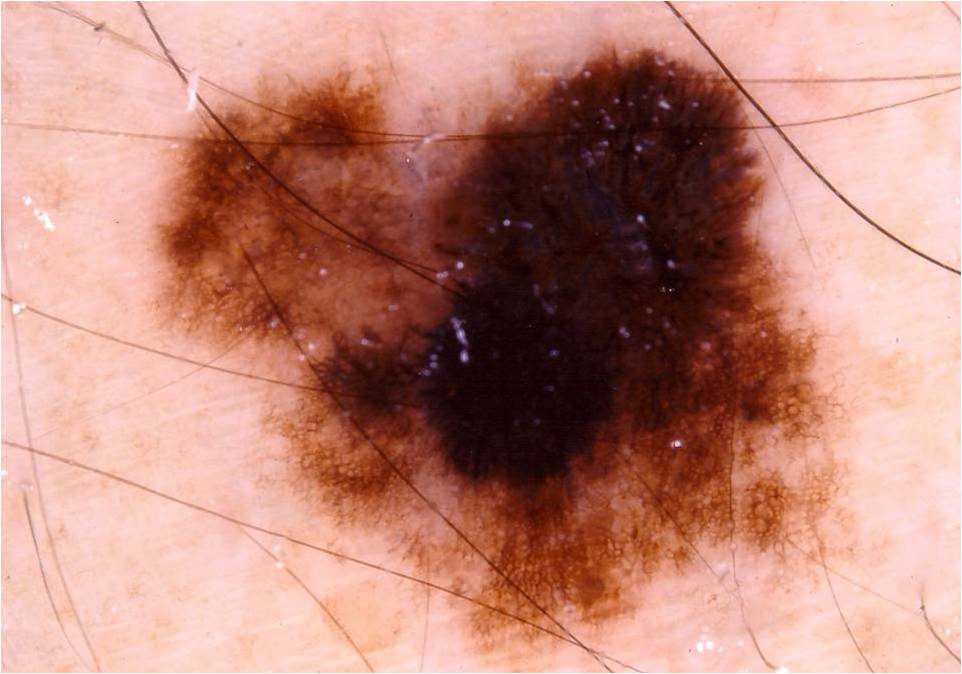subject: male, roughly 45 years of age | image type: dermoscopy of a skin lesion | size: ~49% of the field | location: [145,38,871,664] | features: pigment network and streaks | diagnosis: a melanoma.